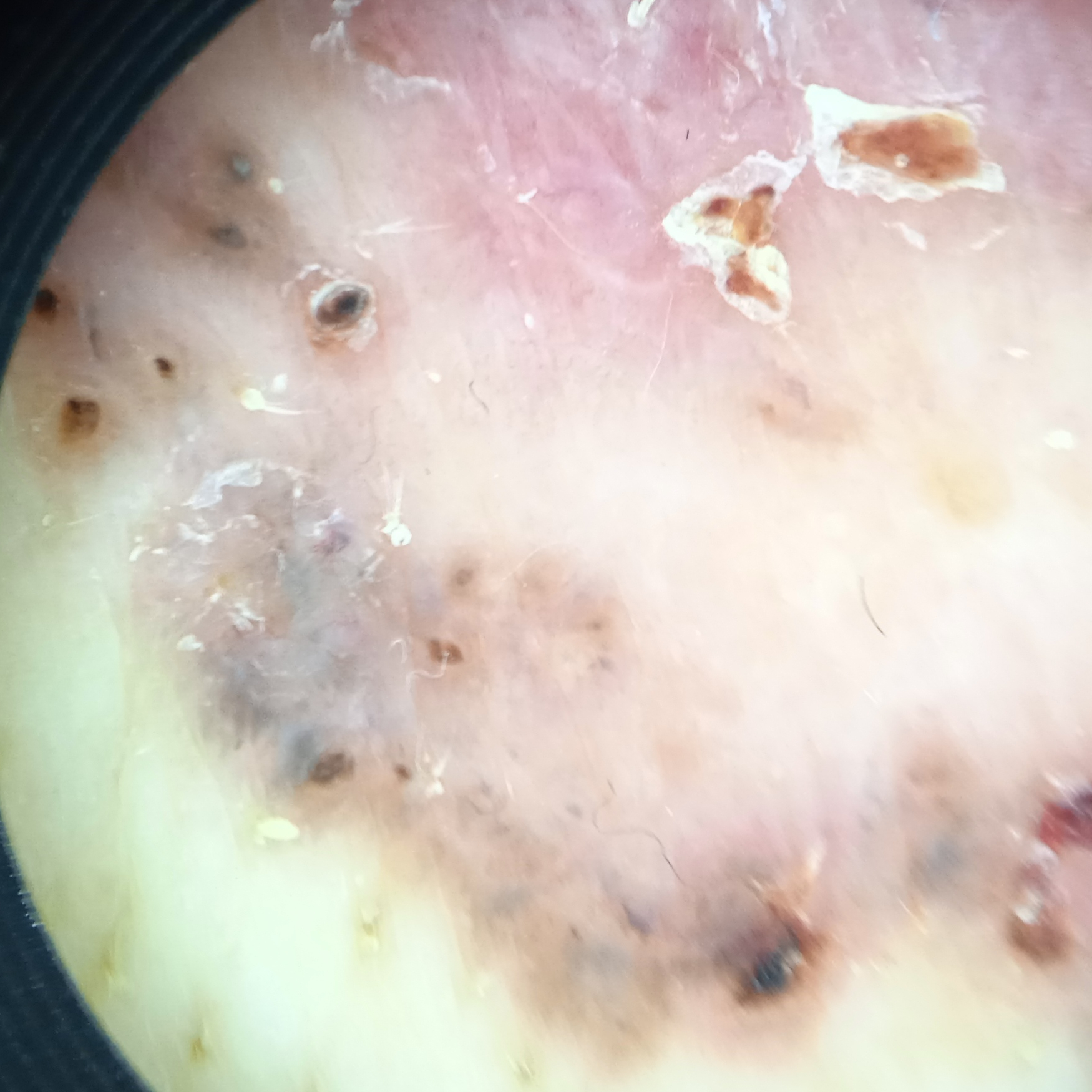<case>
  <referral>clinical suspicion of basal cell carcinoma</referral>
  <patient>
    <age>65</age>
    <sex>male</sex>
  </patient>
  <image>dermatoscopic image</image>
  <lesion_location>the torso</lesion_location>
  <lesion_size>
    <diameter_mm>66.0</diameter_mm>
  </lesion_size>
  <diagnosis>
    <name>basal cell carcinoma</name>
    <malignancy>malignant</malignancy>
    <procedure>punch biopsy</procedure>
    <tumor_thickness_mm>0.3</tumor_thickness_mm>
  </diagnosis>
</case>